The patient notes the condition has been present for less than one week; the affected area is the leg; symptoms reported: itching; the patient considered this a rash; this image was taken at an angle:
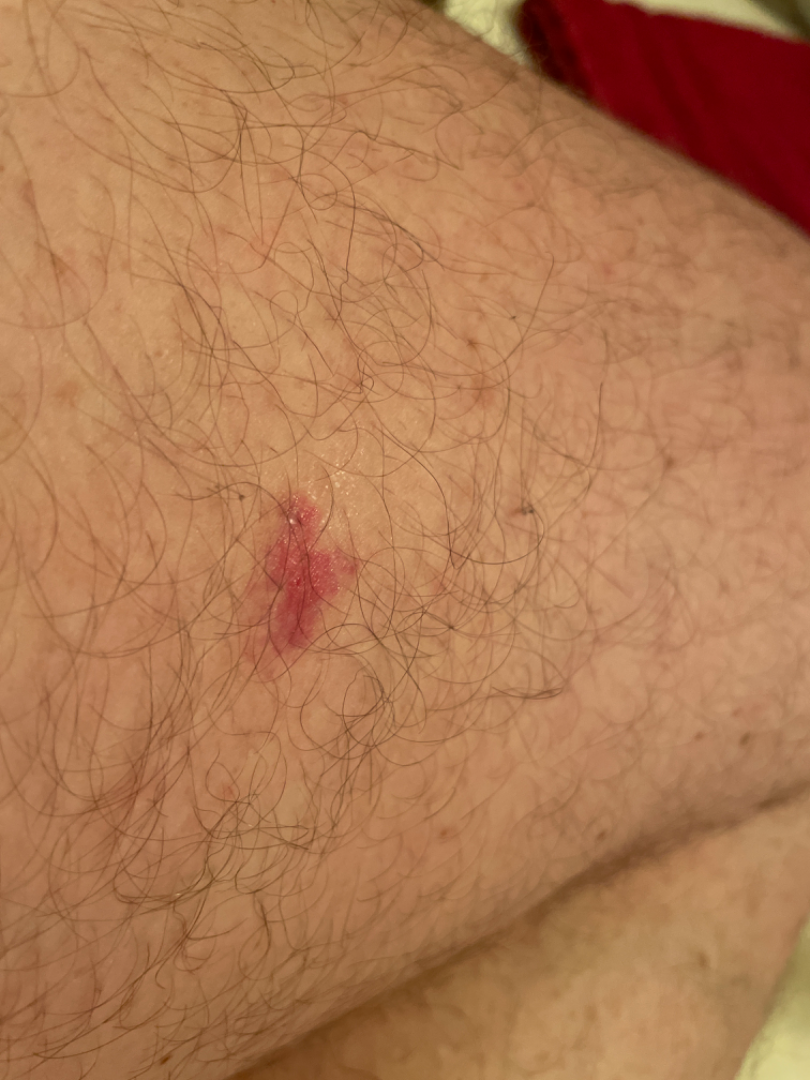Impression: On remote dermatologist review, Allergic Contact Dermatitis (0.50); Basal Cell Carcinoma (0.50).